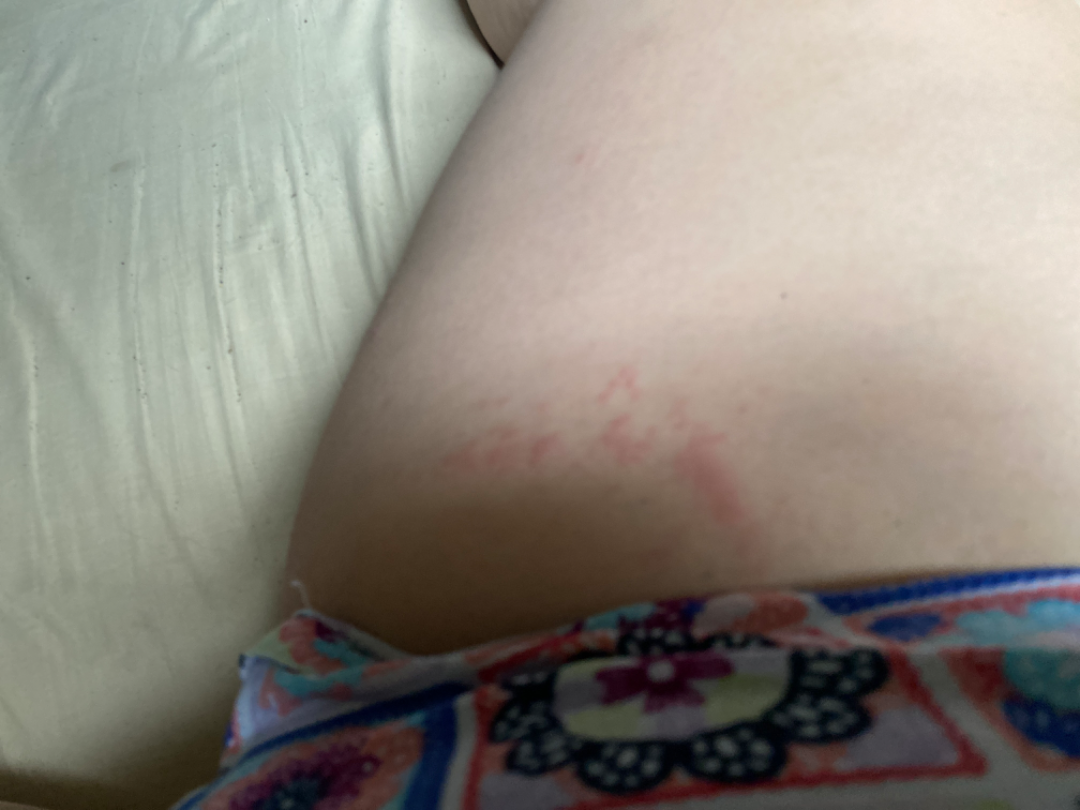The patient notes the lesion is flat.
The lesion is associated with itching.
Self-categorized by the patient as a rash.
The photograph was taken at a distance.
The contributor is 18–29, female.
The condition has been present for less than one week.
The reviewing panel's impression was: Urticaria (primary); Allergic Contact Dermatitis (possible); Herpes Zoster (possible); Acute dermatitis, NOS (lower probability); Insect Bite (lower probability).